A dermoscopy image of a single skin lesion; a female patient roughly 15 years of age: 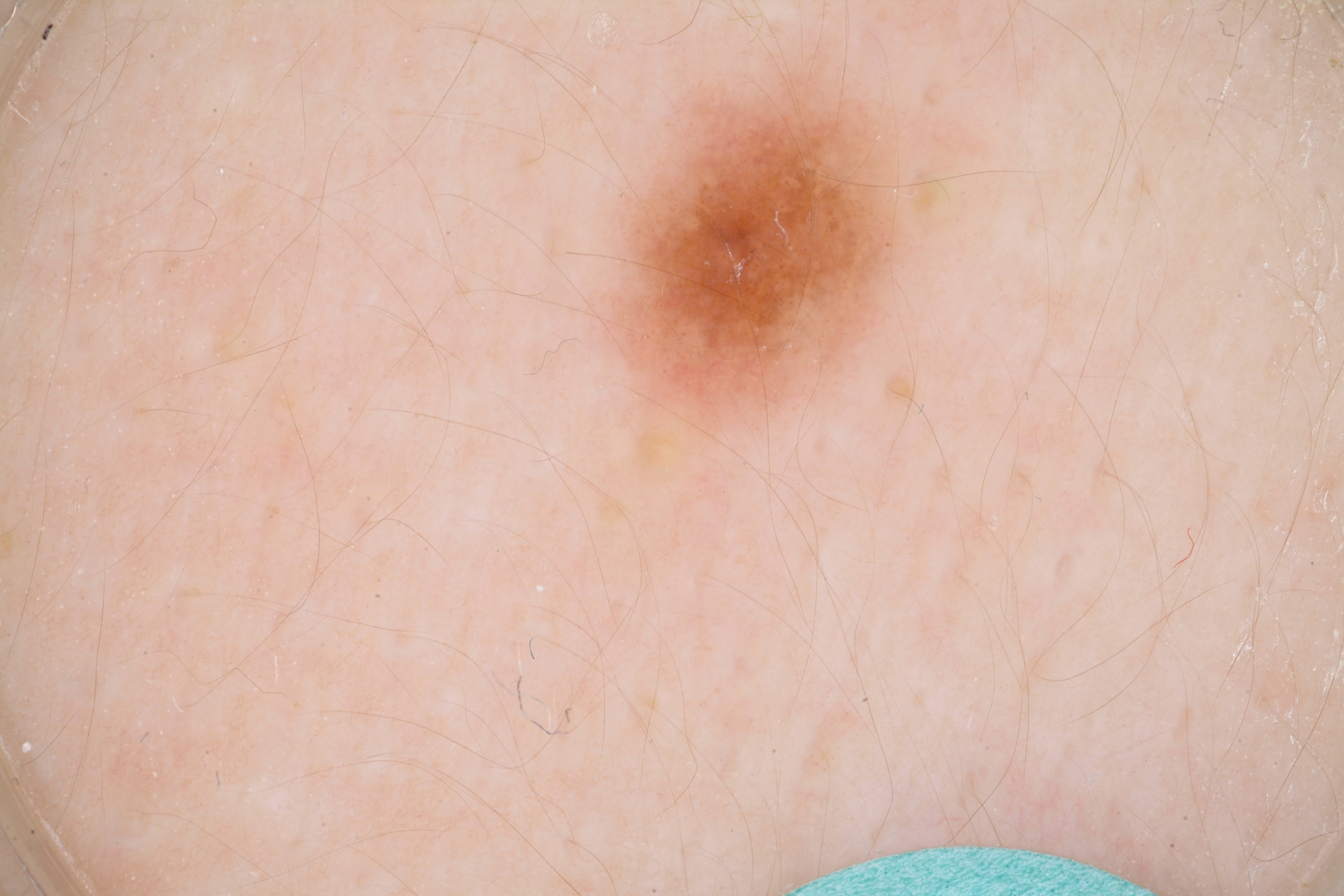The lesion takes up about 6% of the image. Dermoscopy demonstrates no milia-like cysts, globules, streaks, negative network, or pigment network. In (x1, y1, x2, y2) order, the visible lesion spans (613, 67, 907, 438). The diagnostic assessment was a melanocytic nevus, a benign lesion.